A dermatoscopic image of a skin lesion.
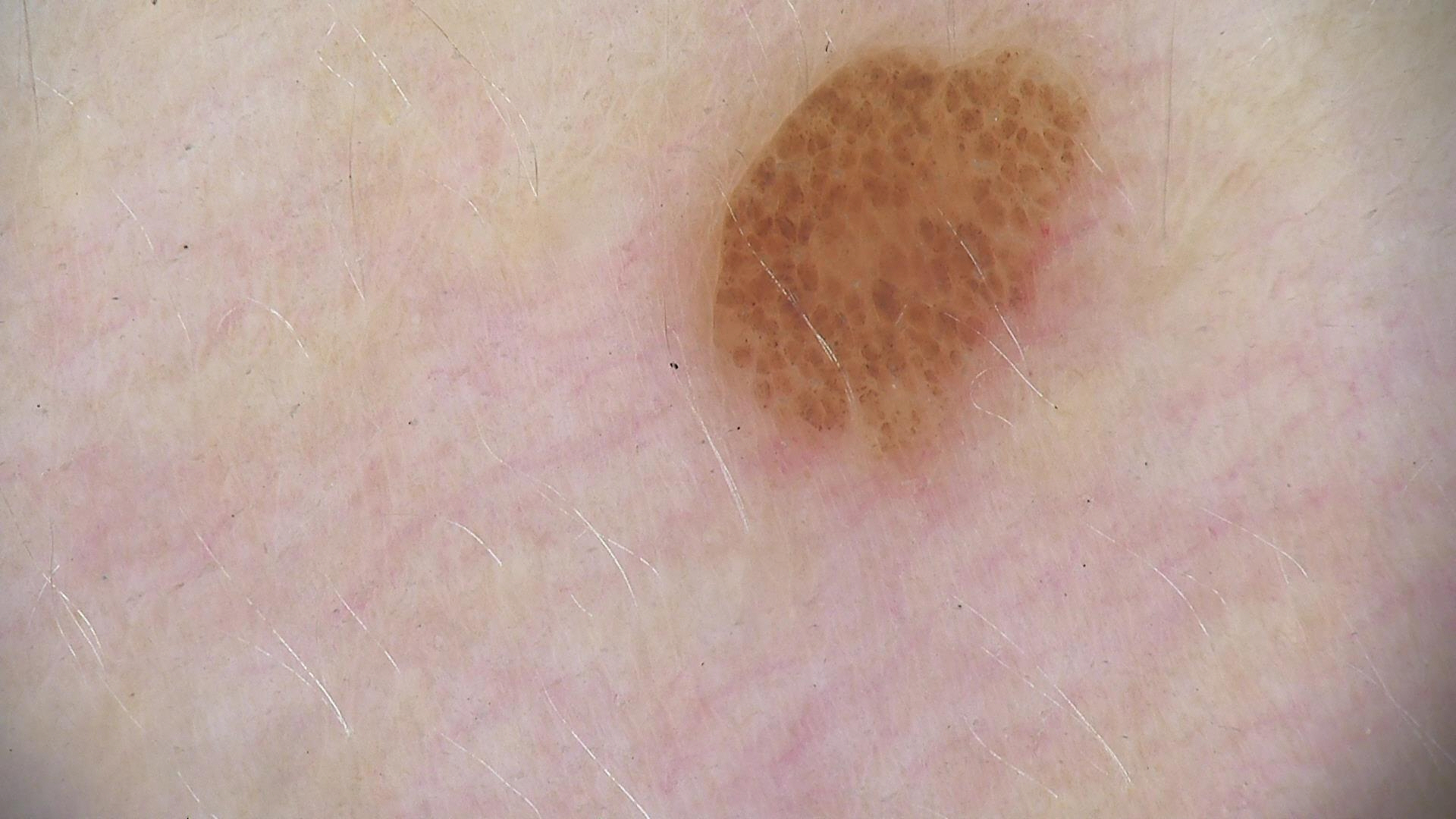<dermoscopy>
  <lesion_type>
    <main_class>banal</main_class>
    <pattern>compound</pattern>
  </lesion_type>
  <diagnosis>
    <name>compound nevus</name>
    <code>cb</code>
    <malignancy>benign</malignancy>
    <super_class>melanocytic</super_class>
    <confirmation>expert consensus</confirmation>
  </diagnosis>
</dermoscopy>